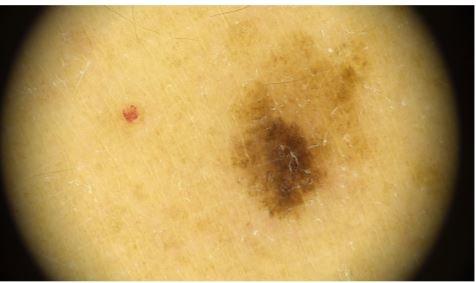Summary:
A female patient roughly 45 years of age. A dermoscopy image of a single skin lesion. The lesion is located on an upper extremity.
Conclusion:
Histopathologically confirmed as a melanoma.